A dermatoscopic image of a skin lesion.
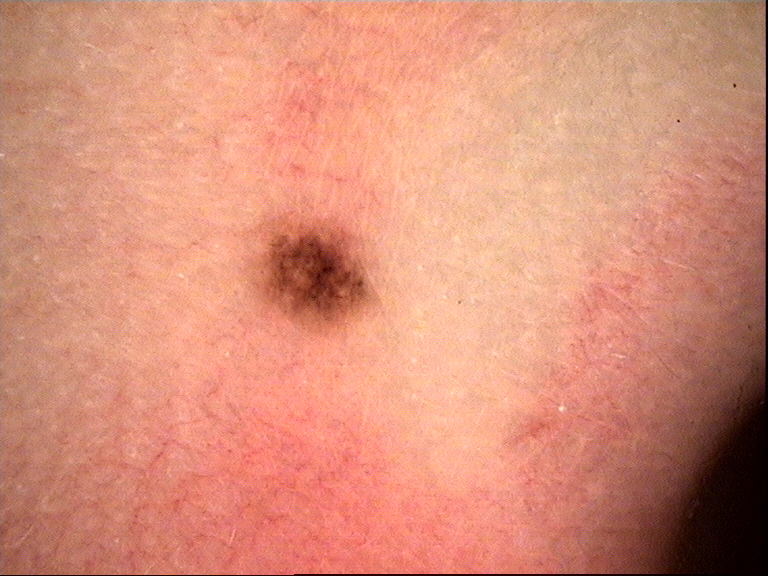The morphology is that of a banal, compound lesion. Classified as a Miescher nevus.